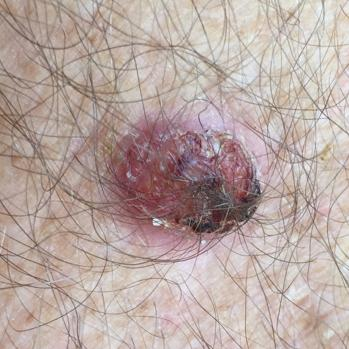A male subject aged 54. By history, prior skin cancer (patient or family), pesticide exposure, alcohol use, and prior malignancy (patient or family). The patient was assessed as Fitzpatrick skin type II. A clinical photo of a skin lesion taken with a smartphone. Located on an arm. The lesion measures 15 × 12 mm. The patient reports that the lesion hurts, has bled, is elevated, has grown, and itches, but has not changed. Histopathological examination showed a malignant lesion — a basal cell carcinoma.